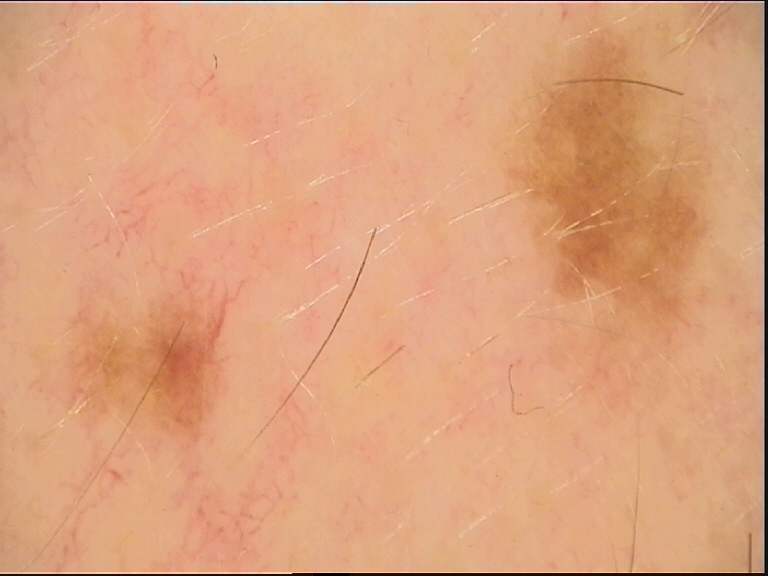diagnostic label = dysplastic junctional nevus (expert consensus).